The palm, head or neck, back of the hand, back of the torso, front of the torso and arm are involved; the patient considered this a rash; the patient reports the lesion is flat and raised or bumpy; the condition has been present for about one day; the patient is a female aged 18–29; the lesion is associated with burning, bothersome appearance and itching; the photo was captured at a distance; the patient reported no systemic symptoms: 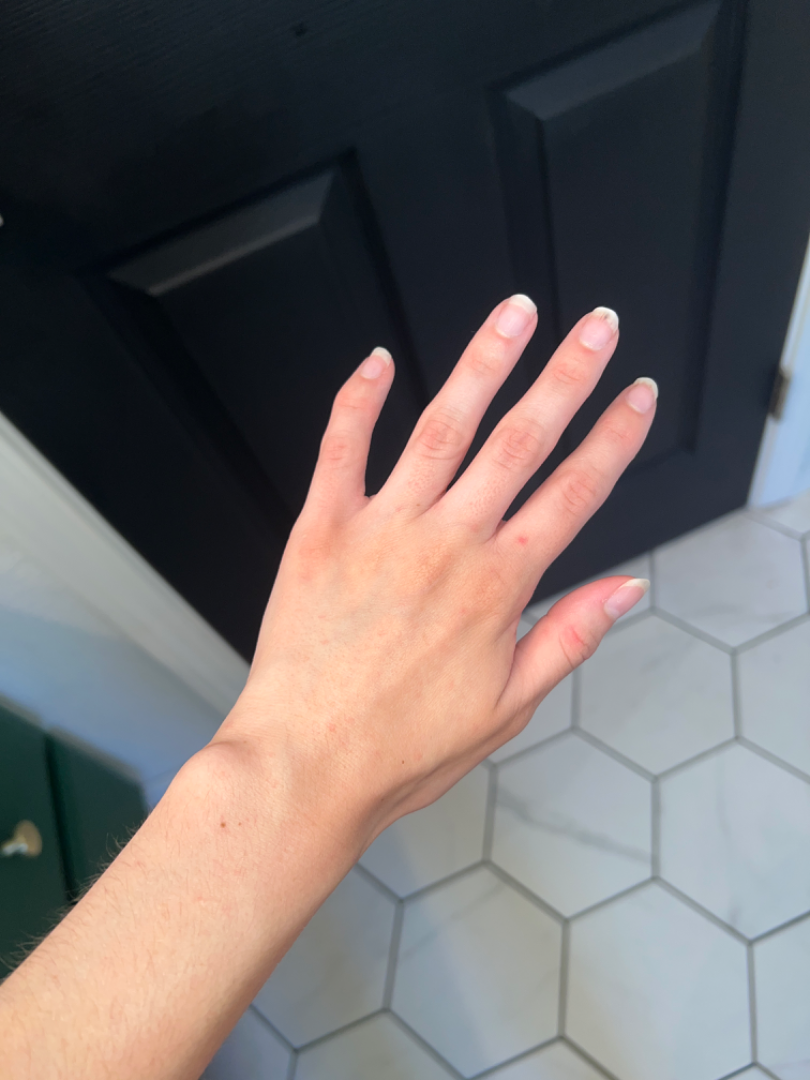differential — most consistent with Insect Bite.